A dermoscopic photograph of a skin lesion.
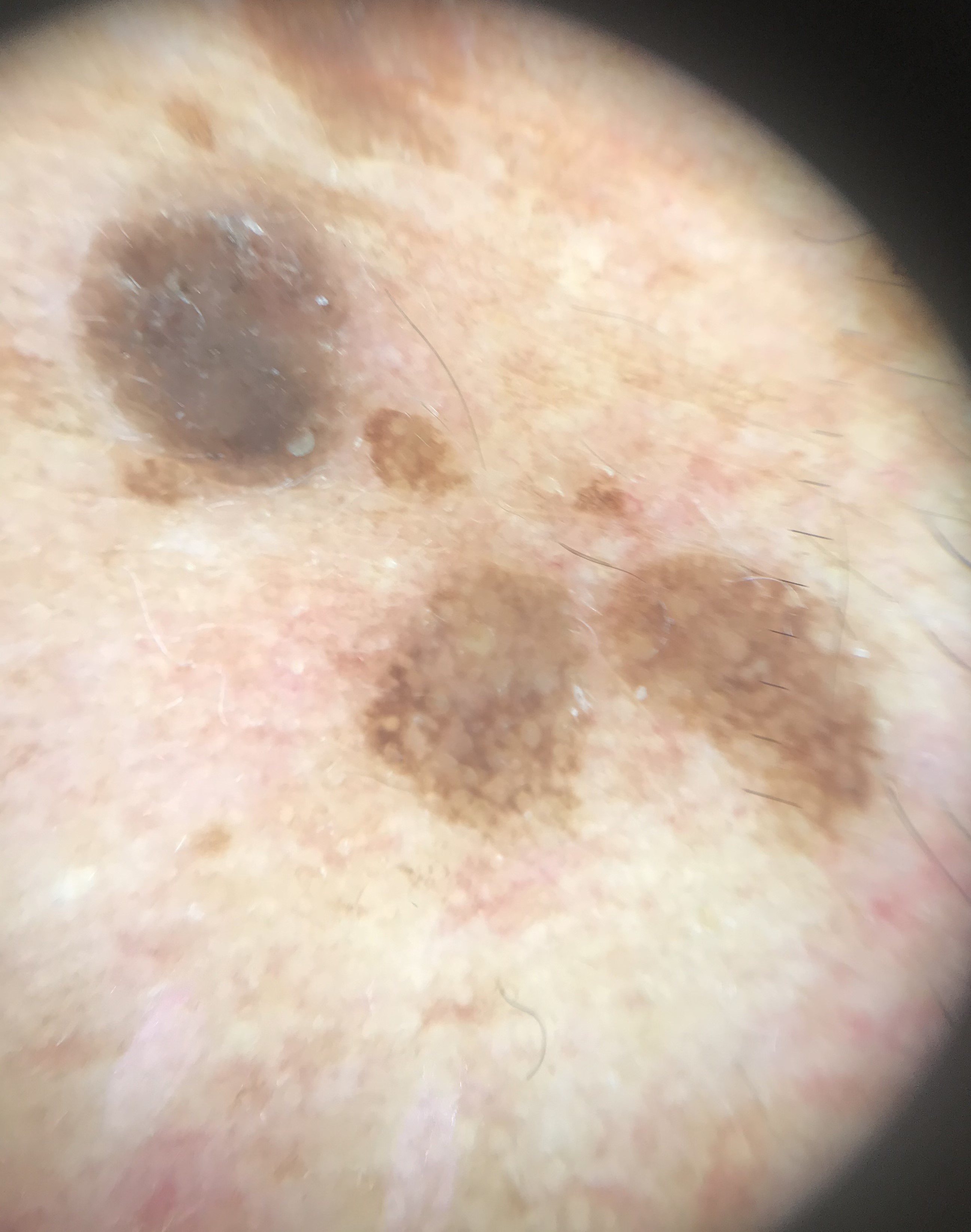This is a keratinocytic lesion.
Labeled as a seborrheic keratosis.